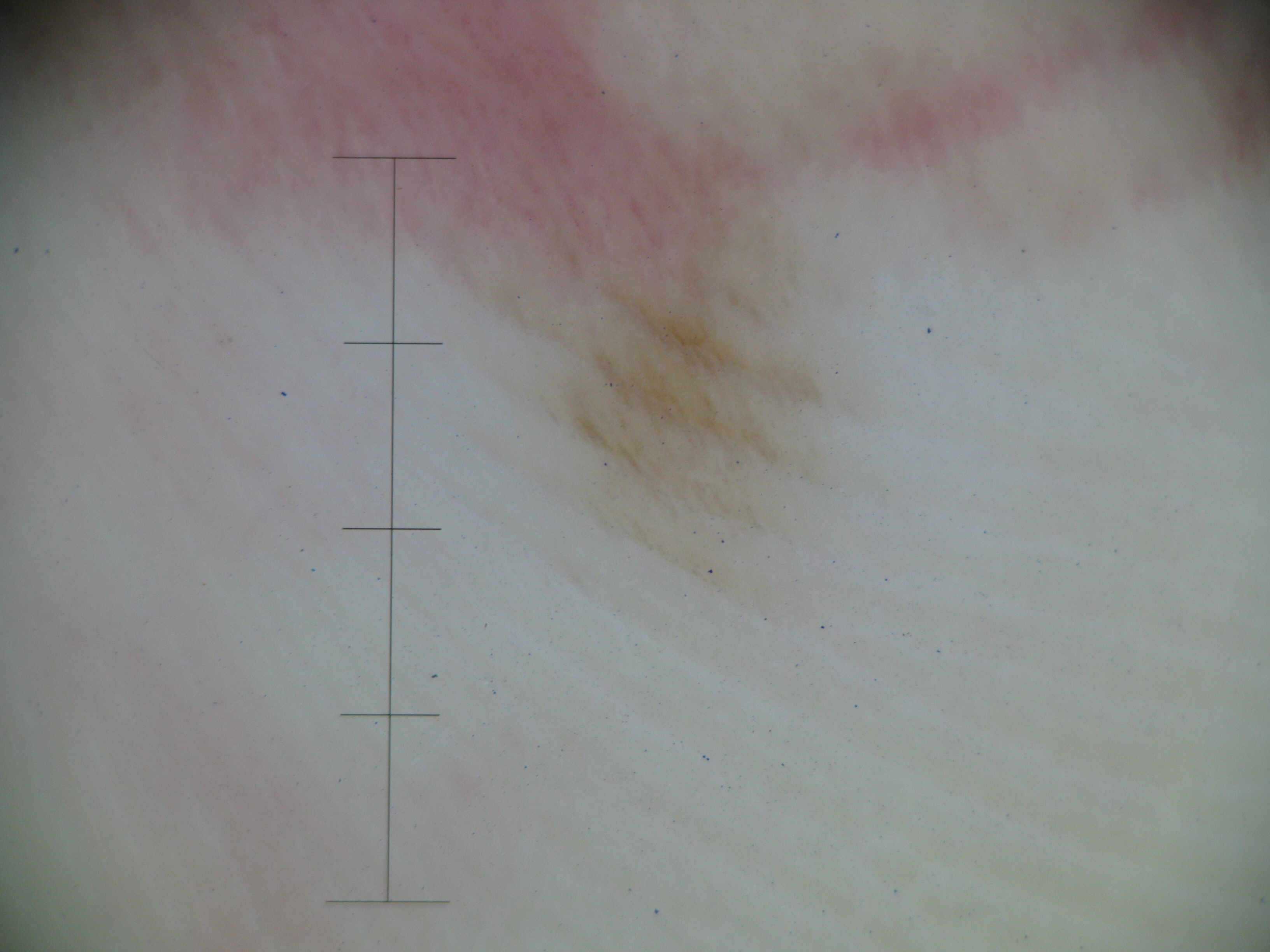Findings:
• class: acral junctional nevus (expert consensus)